A skin lesion imaged with a dermatoscope.
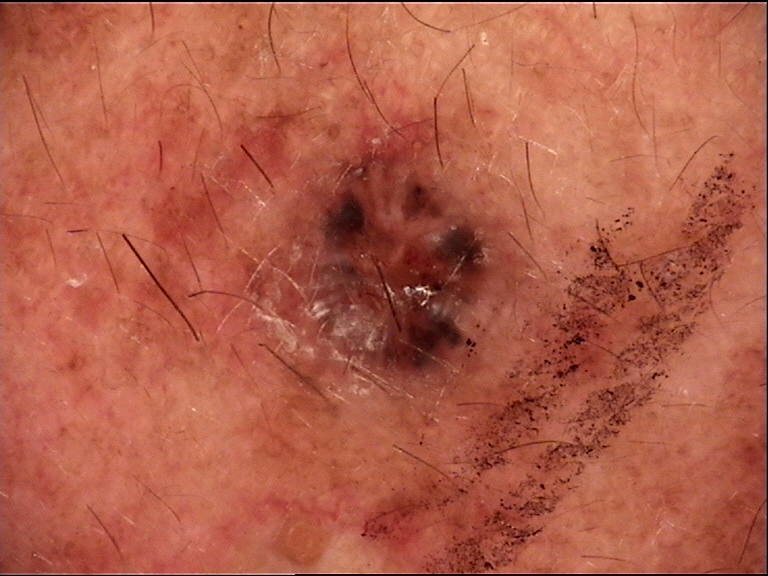The biopsy diagnosis was a basal cell carcinoma.